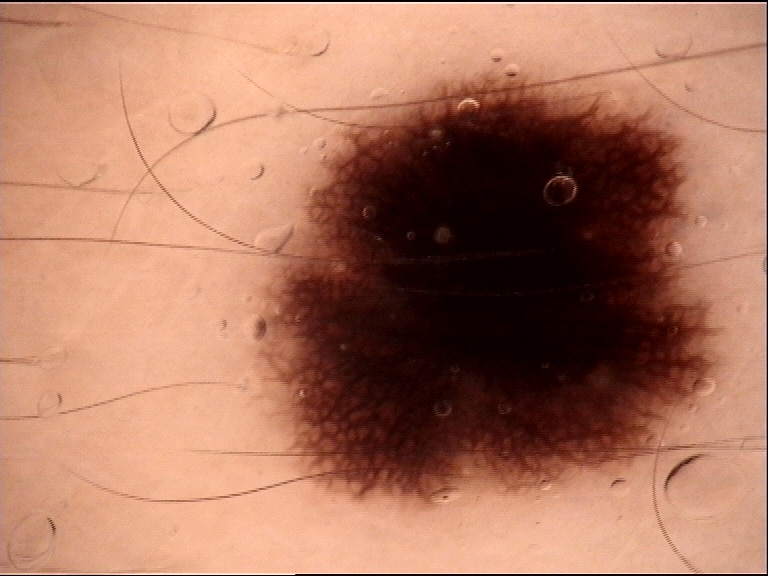  image: dermatoscopy
  diagnosis:
    name: Spitz/Reed nevus
    code: srjd
    malignancy: benign
    super_class: melanocytic
    confirmation: expert consensus